Dermoscopy of a skin lesion: 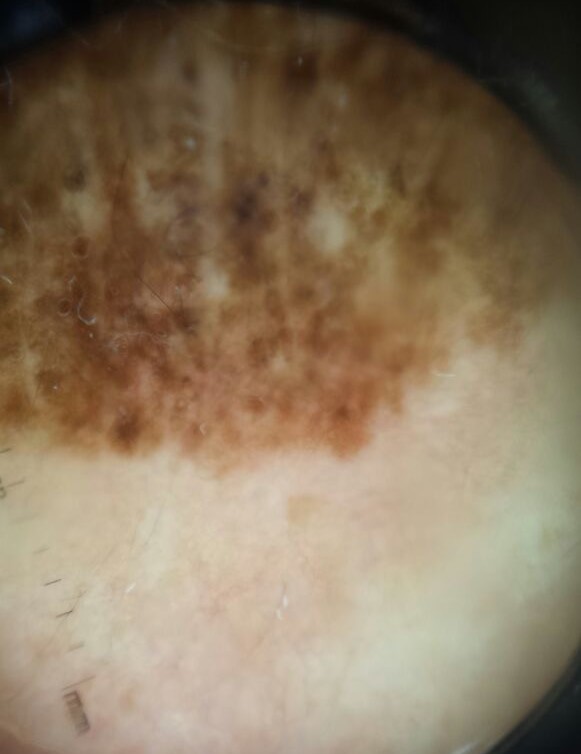Case:
* assessment: congenital dysplastic compound nevus (expert consensus)